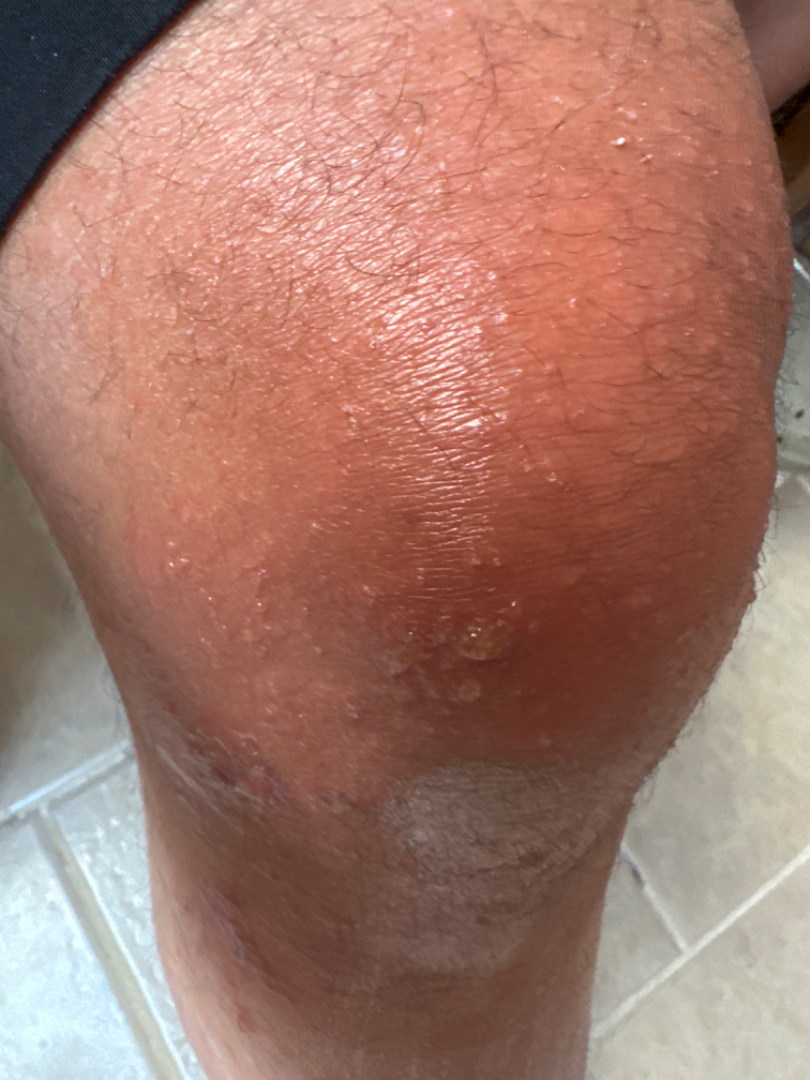{"shot_type": "at a distance", "body_site": ["top or side of the foot", "back of the torso", "arm", "head or neck", "leg"], "differential": {"tied_lead": ["Impetigo", "Psoriasis", "Allergic Contact Dermatitis"]}}